The lesion is described as raised or bumpy. Self-categorized by the patient as skin that appeared healthy to them. No relevant lesion symptoms reported. Located on the leg. Close-up view. The contributor is a female aged 60–69. Skin tone: self-reported Fitzpatrick skin type III; human graders estimated a MST of 2. Present for about one day:
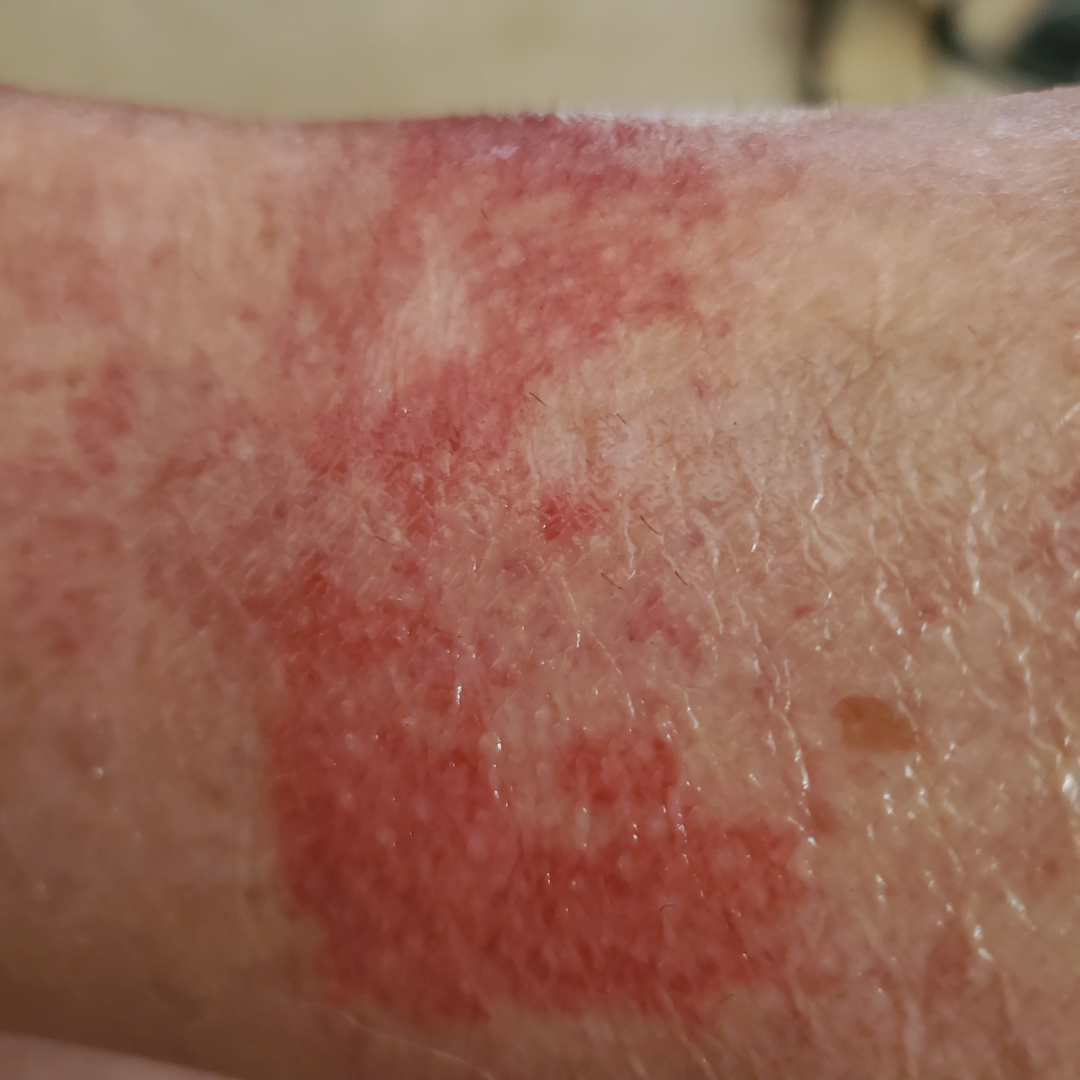Findings:
The image was not sufficient for the reviewer to characterize the skin condition.